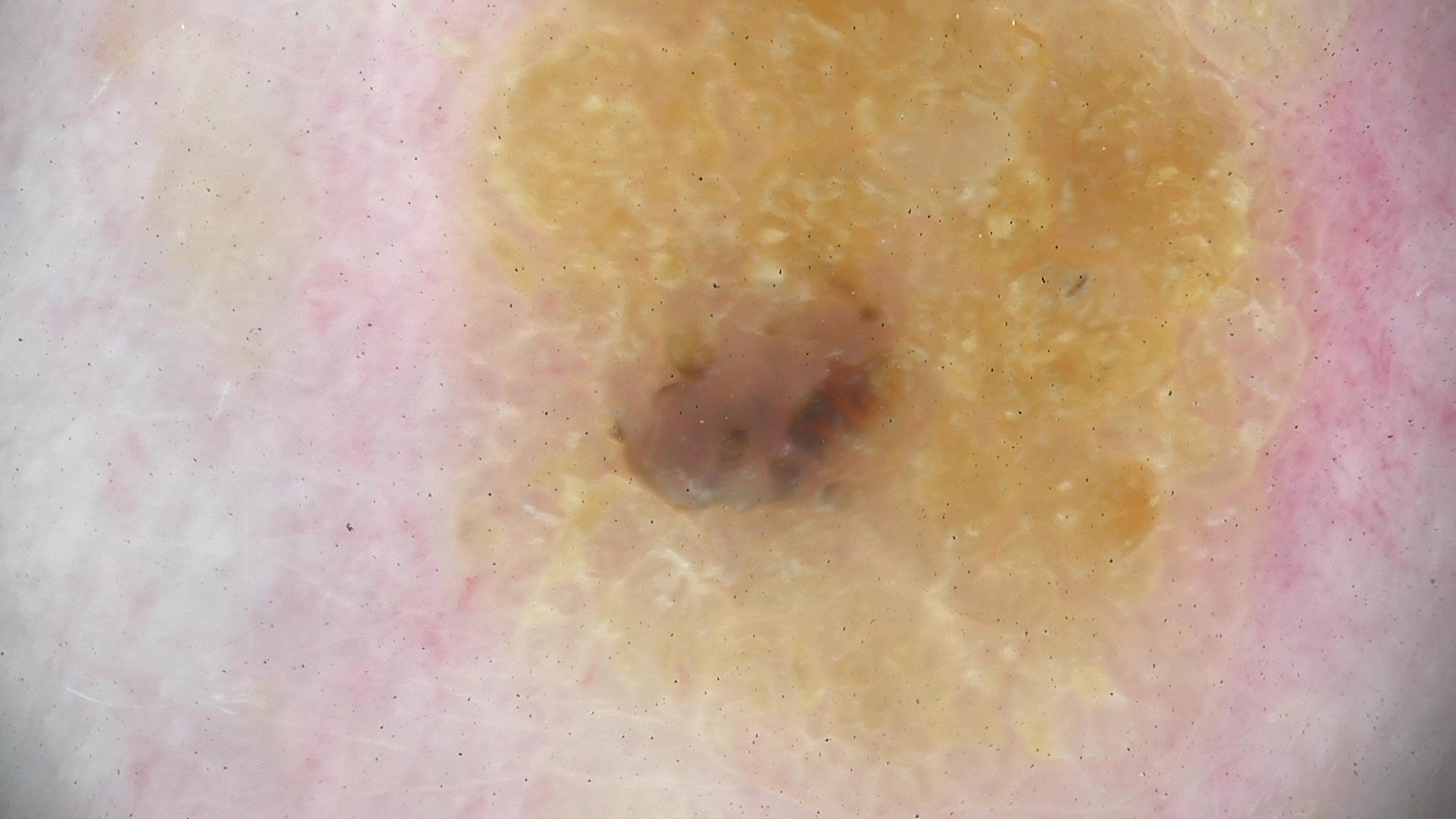Impression: Consistent with a benign, keratinocytic lesion — a seborrheic keratosis.